A patient aged 52:
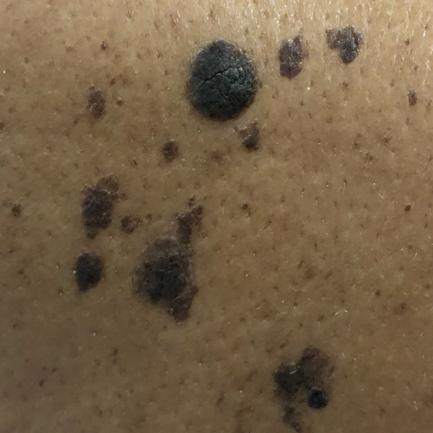The lesion was found on the back.
Per patient report, the lesion is elevated.
Consistent with a seborrheic keratosis.